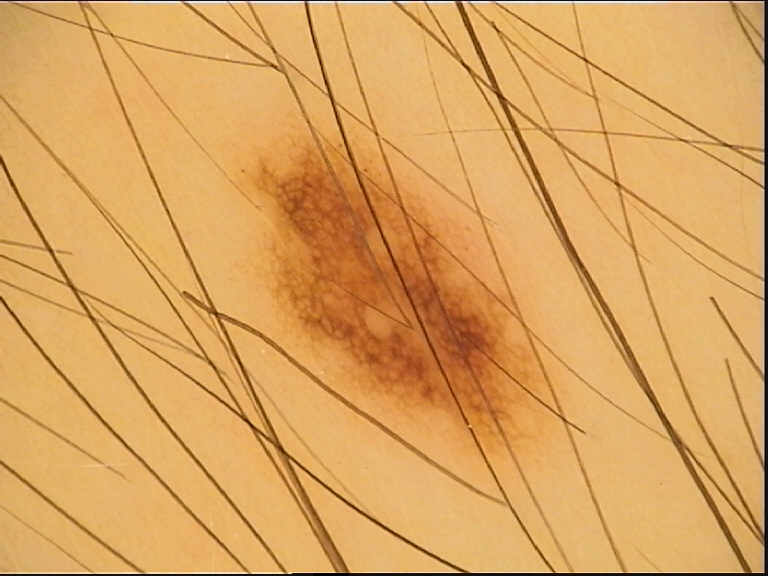Diagnosed as a dysplastic junctional nevus.